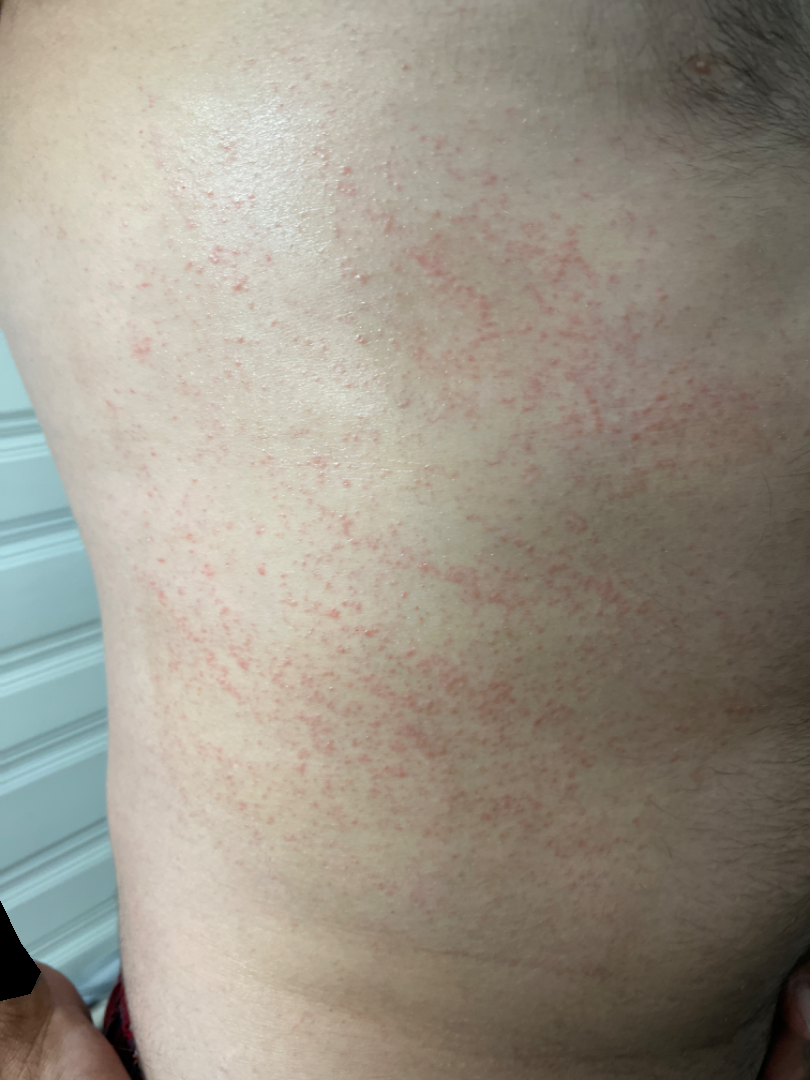A close-up photograph. Miliaria (most likely); Viral Exanthem (considered); Acute dermatitis, NOS (considered).